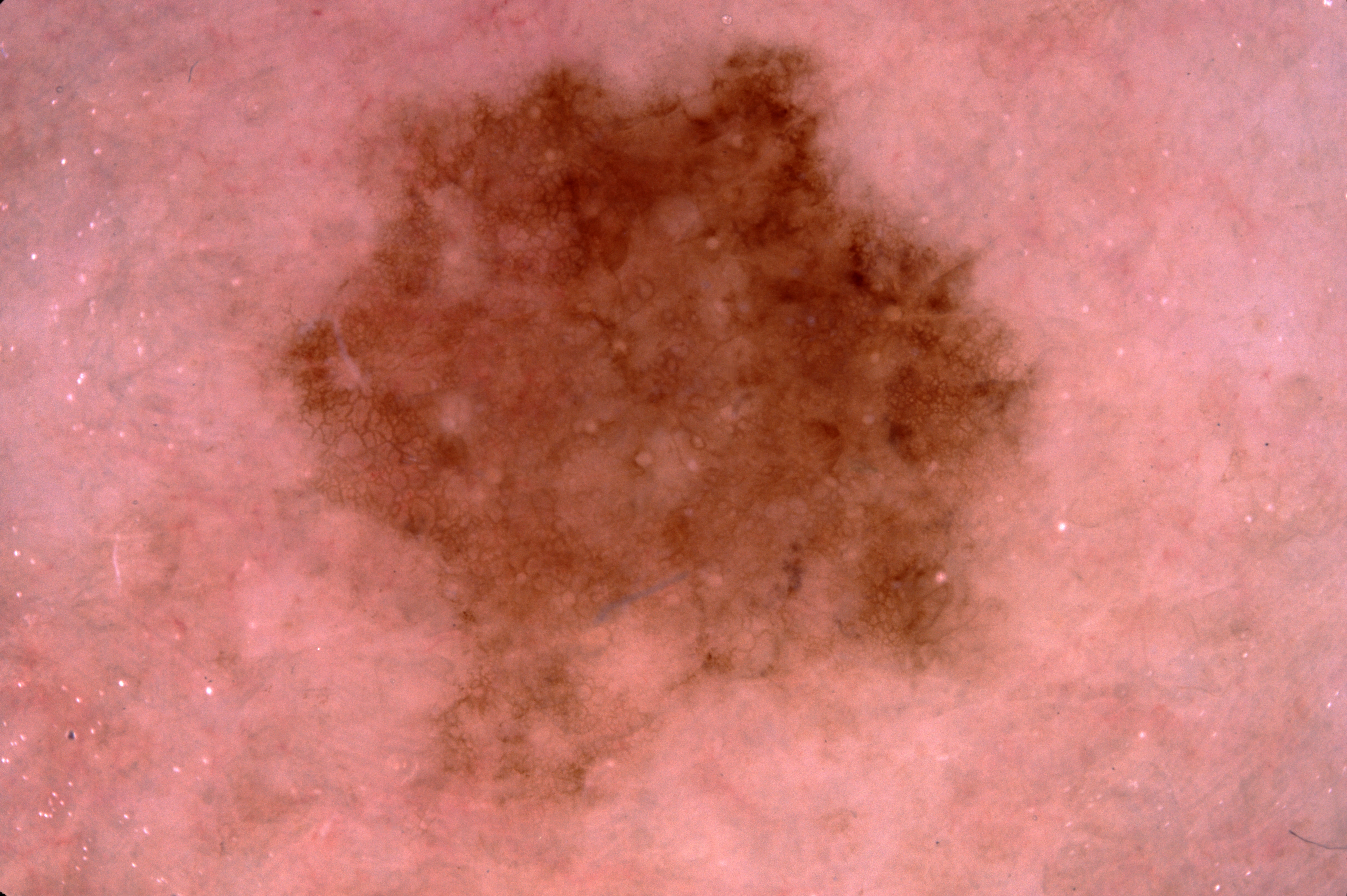Case summary: A dermatoscopic image of a skin lesion. A female patient, about 65 years old. Dermoscopic assessment notes pigment network; no milia-like cysts, negative network, or streaks. The lesion occupies roughly 35% of the field. The lesion extends to the edge of the dermoscopic field. The lesion's extent is x1=220, y1=0, x2=1046, y2=836. Impression: Clinically diagnosed as a melanocytic nevus.